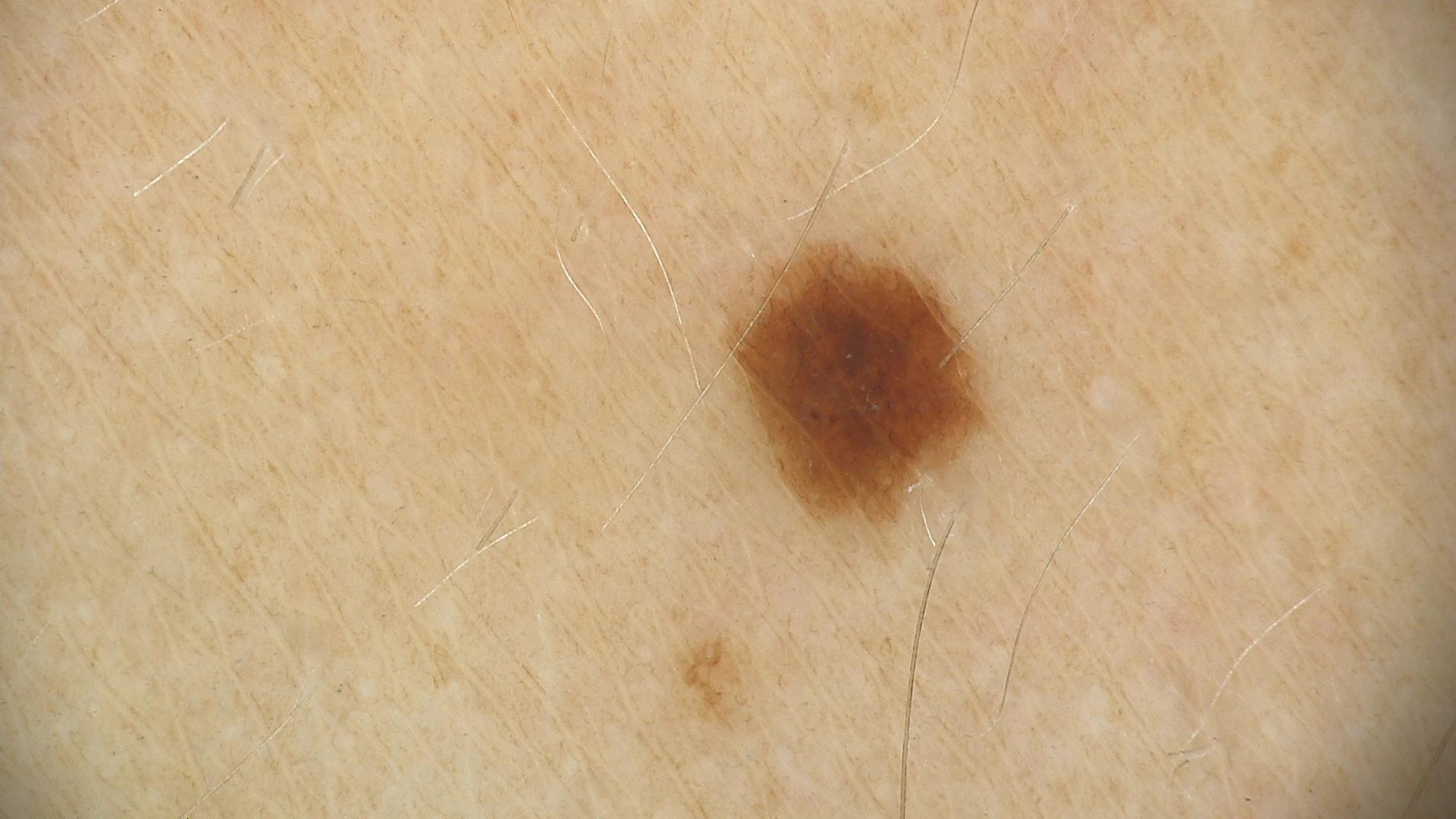A dermoscopic close-up of a skin lesion.
Labeled as a benign lesion — a dysplastic junctional nevus.